The photo was captured at a distance; the subject is a female aged 30–39; located on the top or side of the foot:
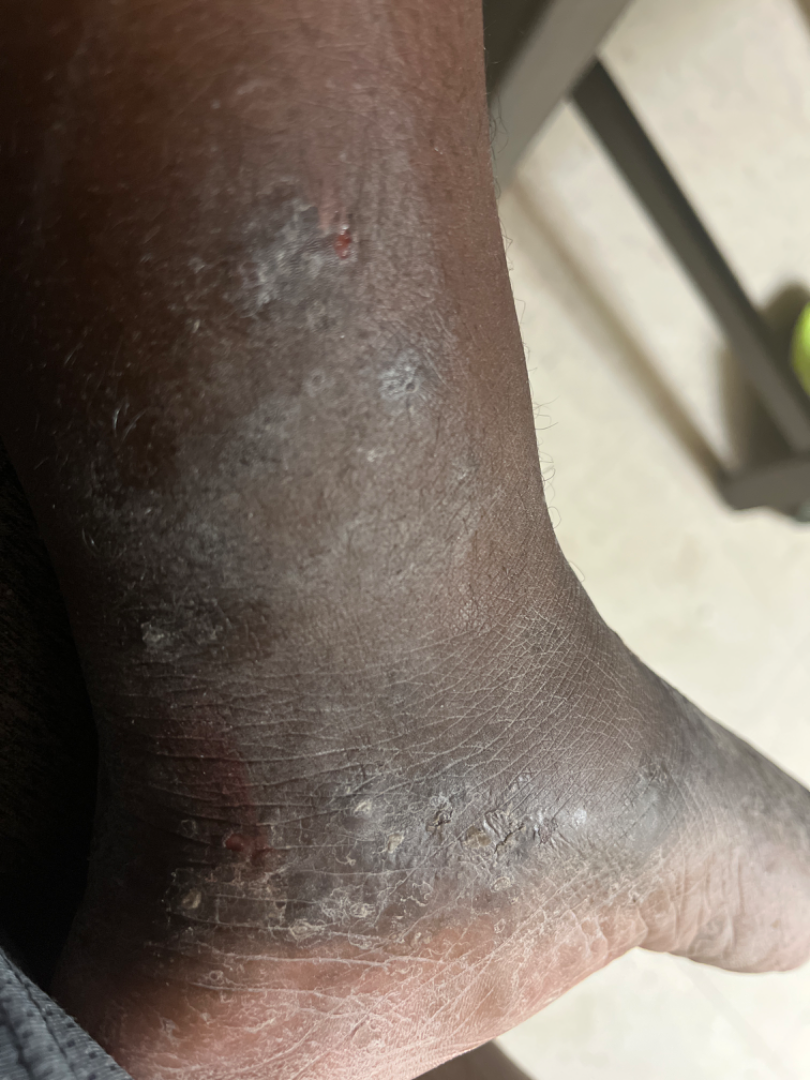{"differential": {"tied_lead": ["Tinea", "Eczema"], "unlikely": ["Psoriasis"]}}